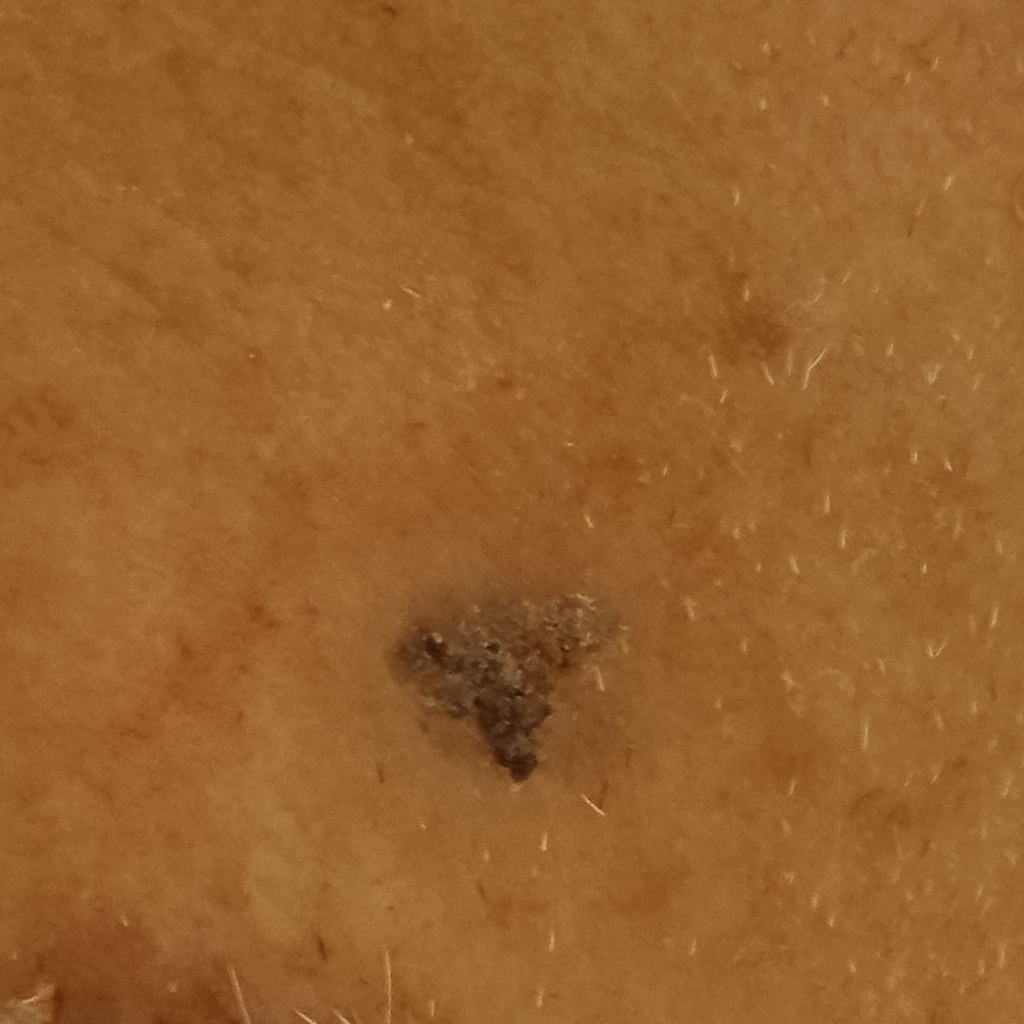Q: What is the patient's nevus burden?
A: few melanocytic nevi overall
Q: Why was this imaged?
A: research study (no referral diagnosis)
Q: What is the imaging modality?
A: clinical photograph
Q: How does the patient's skin react to sun?
A: skin reddens with sun exposure
Q: Where is the lesion?
A: the face
Q: How large is the lesion?
A: 10.5 mm
Q: What was the diagnosis?
A: seborrheic keratosis (dermatologist consensus)